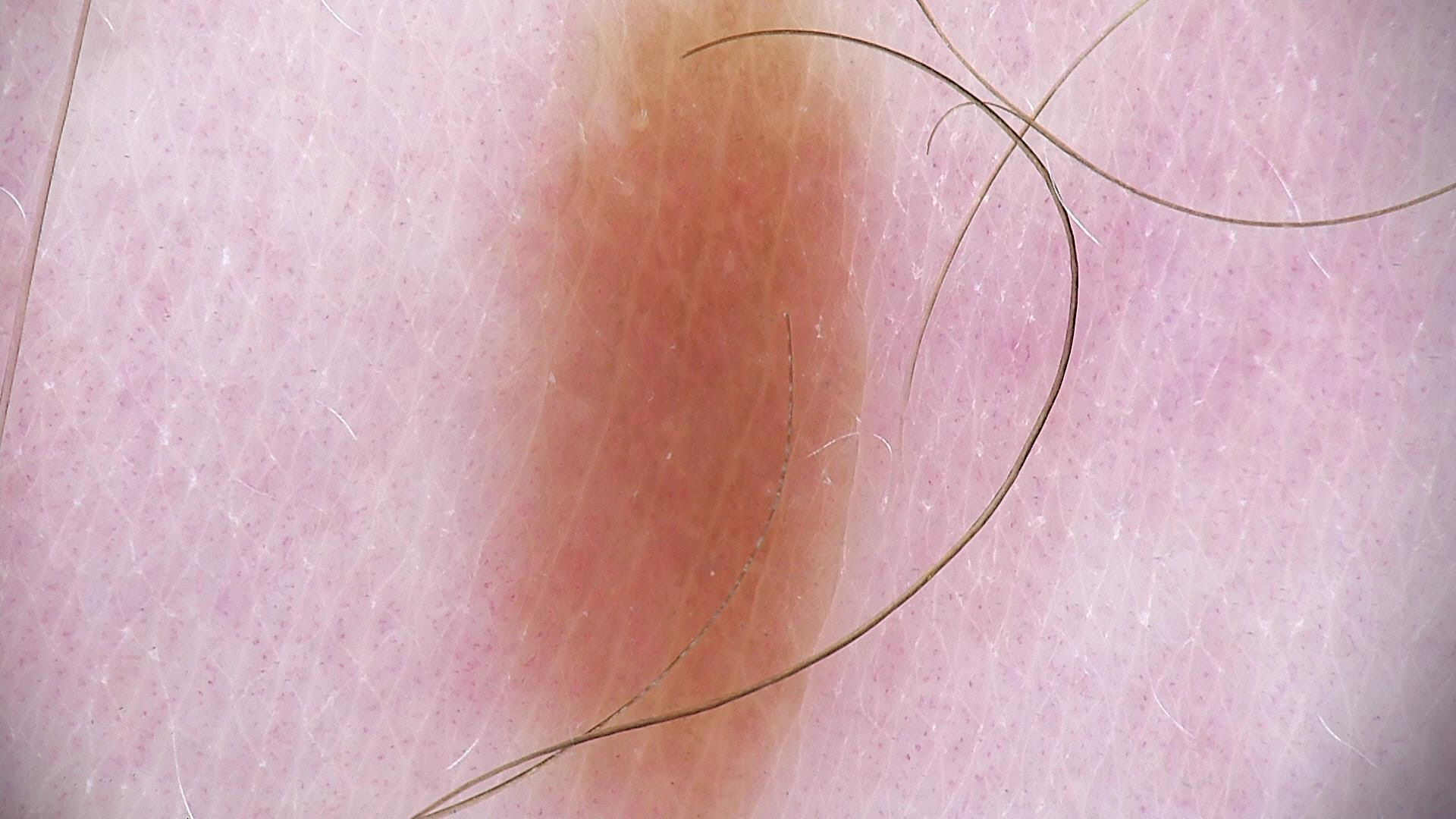A dermoscopic image of a skin lesion. The diagnosis was a benign lesion — an acral dysplastic junctional nevus.